The referring clinician suspected melanoma. A moderate number of moles by the patient's own estimate. A dermatoscopic image of a skin lesion. The patient says their skin reddens painfully with sun exposure. A female patient 50 years old — 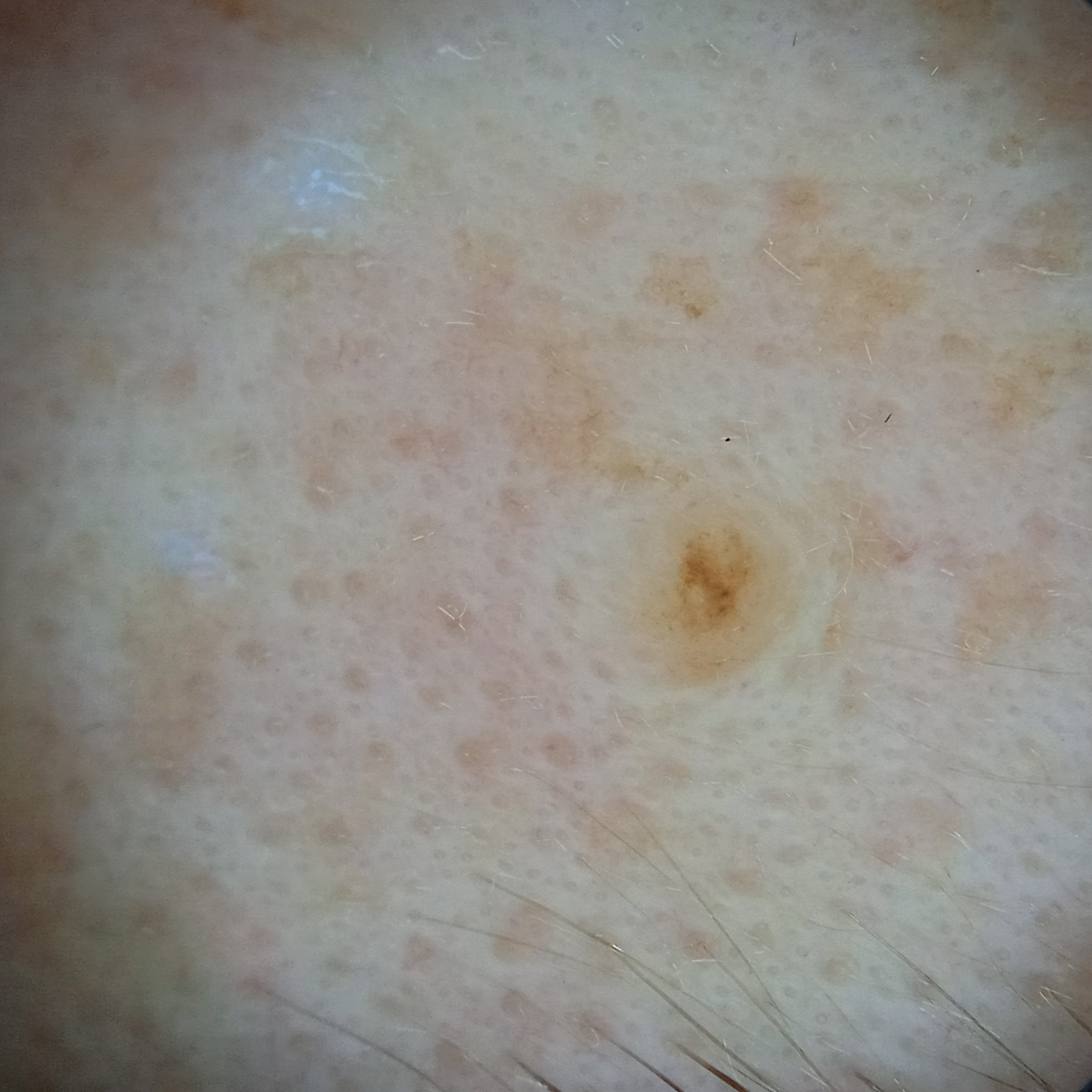body site = the face; diameter = 1.8 mm; assessment = melanocytic nevus (dermatologist consensus).